Dermoscopy of a skin lesion.
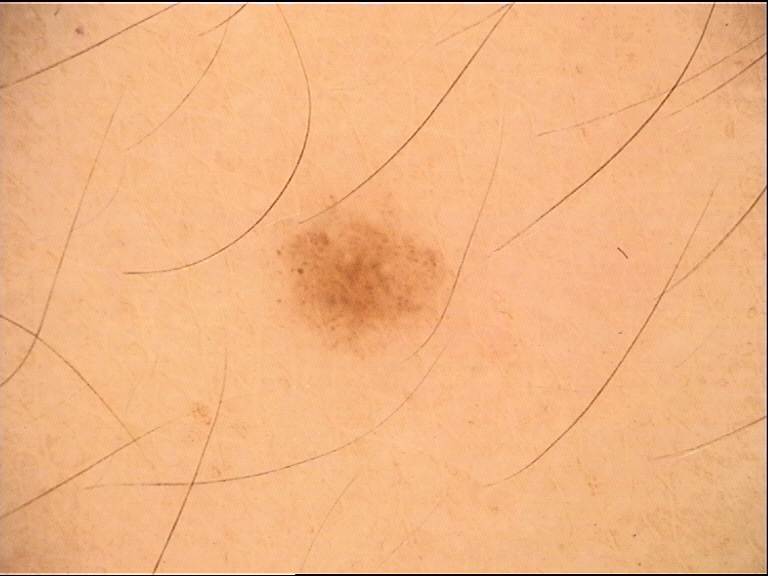<dermoscopy>
<lesion_type>
<main_class>banal</main_class>
<pattern>junctional</pattern>
</lesion_type>
<diagnosis>
<name>junctional nevus</name>
<code>jb</code>
<malignancy>benign</malignancy>
<super_class>melanocytic</super_class>
<confirmation>expert consensus</confirmation>
</diagnosis>
</dermoscopy>